A patient 54 years old — 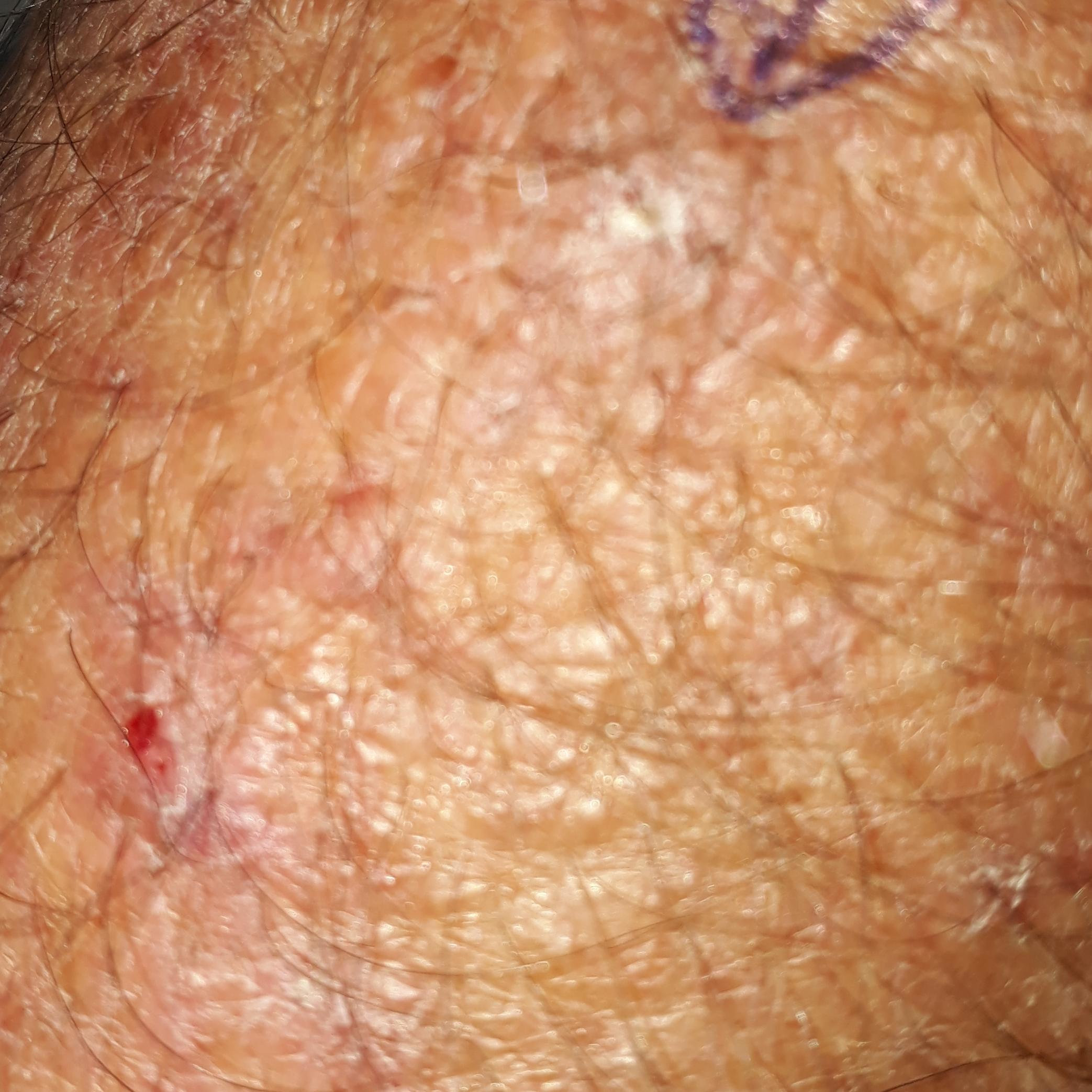The lesion is located on a forearm. By the patient's account, the lesion itches. The clinical impression was an actinic keratosis.